A female subject aged 83 or older · the patient was assessed as Fitzpatrick II.
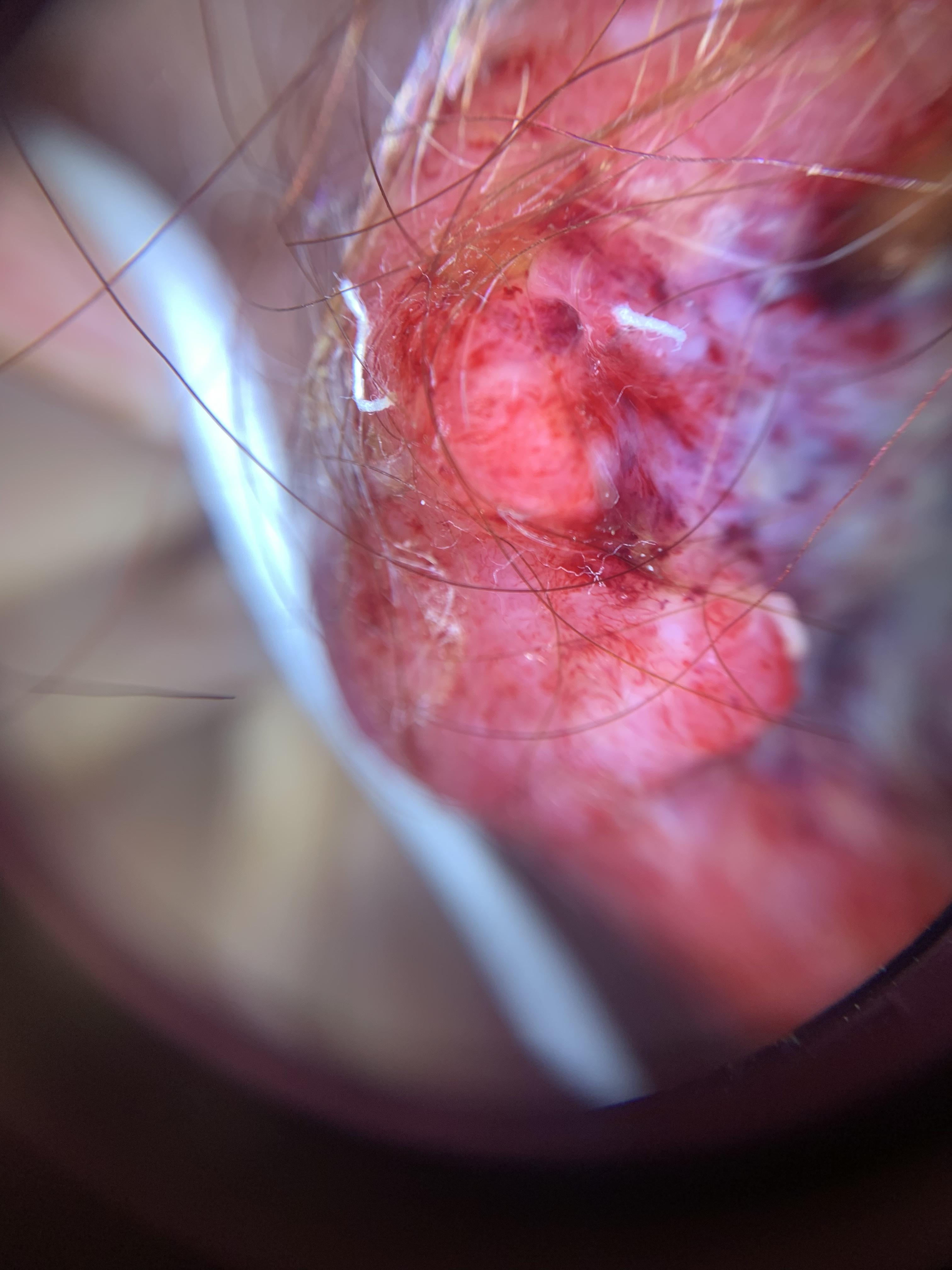anatomic site = the head or neck, diagnostic label = Squamous cell carcinoma (biopsy-proven).